A dermatoscopic image of a skin lesion.
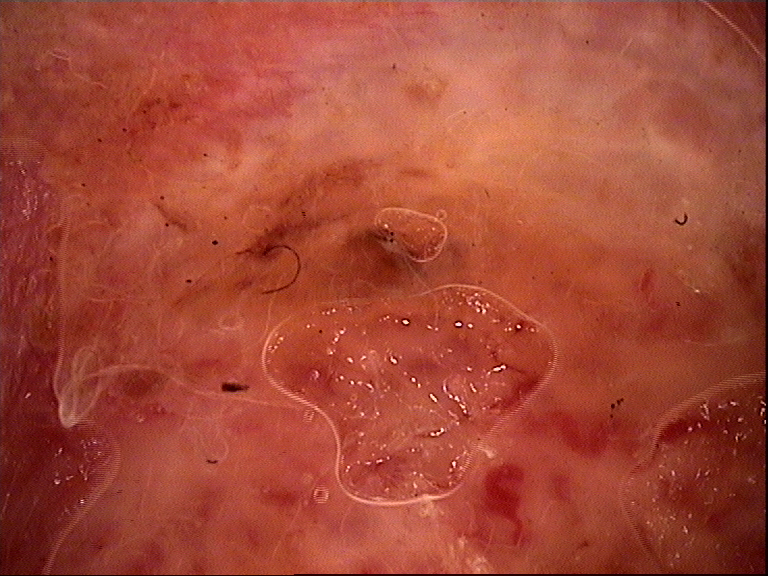The morphology is that of a keratinocytic lesion.
Biopsy-confirmed as a basal cell carcinoma.